The patient described the issue as a rash; an image taken at an angle; the affected area is the arm; the patient notes the condition has been present for one to four weeks; the lesion is described as raised or bumpy; male patient, age 50–59; the lesion is associated with enlargement and pain — 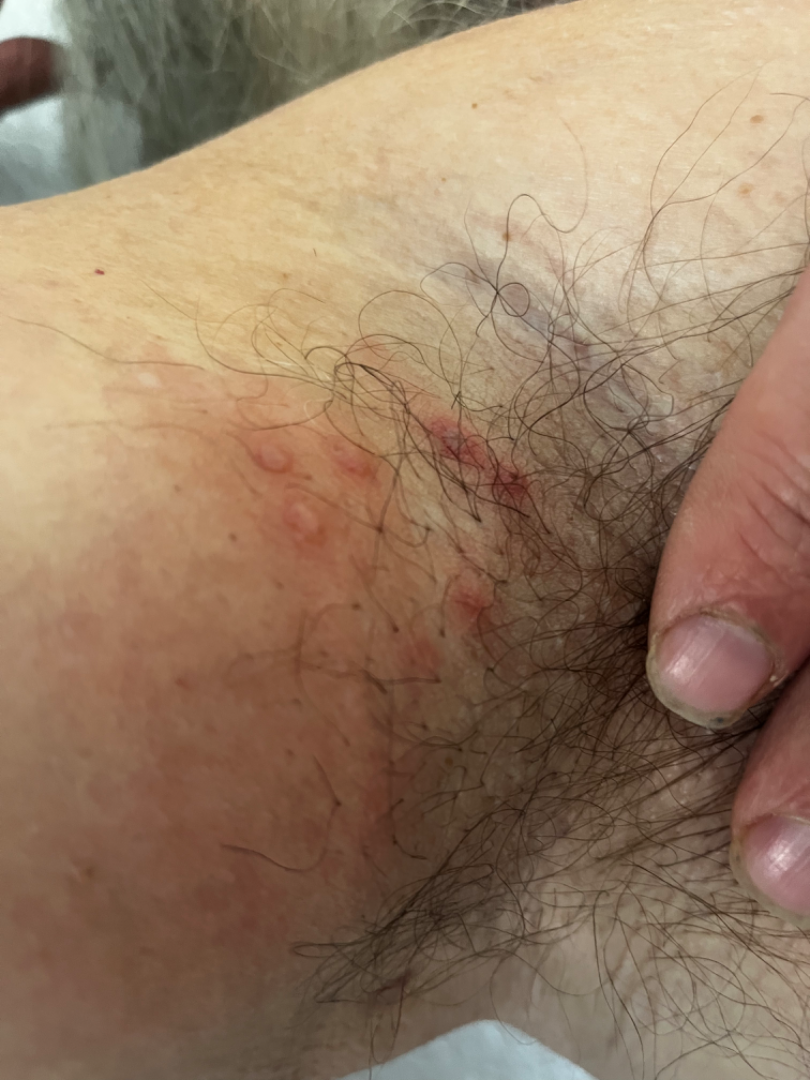On dermatologist assessment of the image, Impetigo and Herpes Zoster were considered with similar weight; a remote consideration is Allergic Contact Dermatitis.